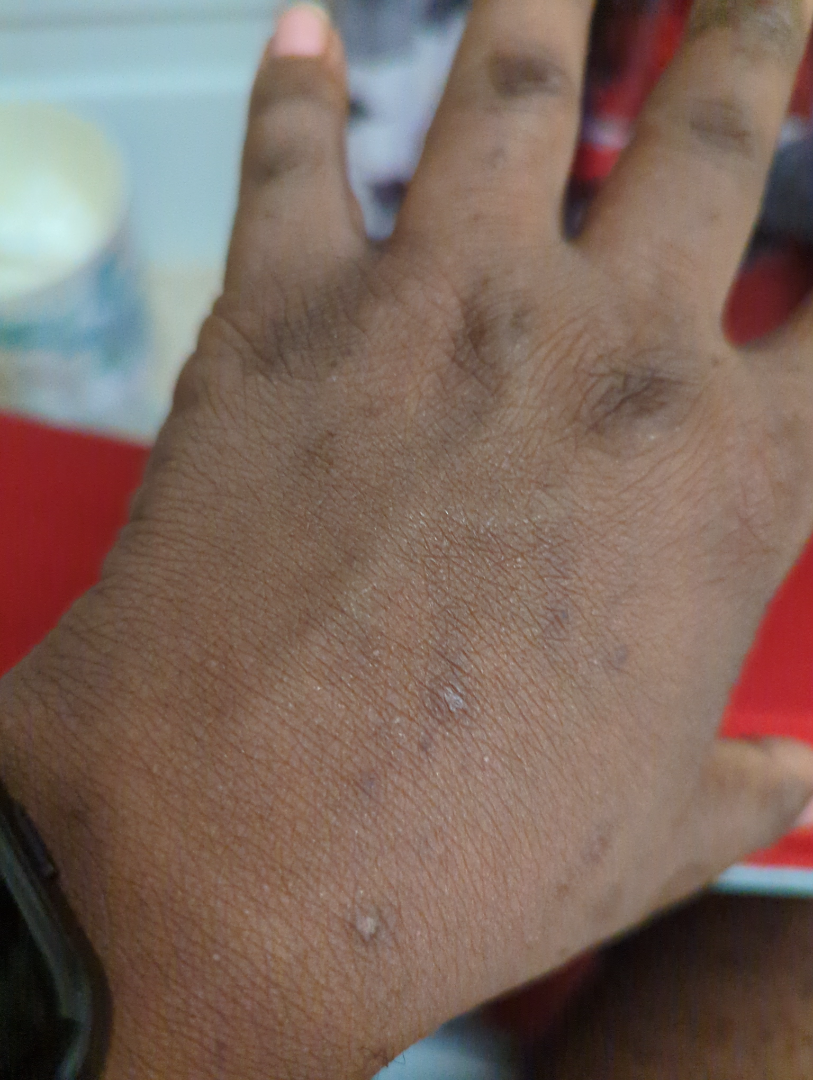Impression: No differential diagnosis could be assigned on photographic review. History: Close-up view. The contributor reports the lesion is raised or bumpy. The lesion is associated with itching. The patient described the issue as skin that appeared healthy to them. The affected area is the leg, sole of the foot and back of the hand. Skin tone: Fitzpatrick skin type VI.